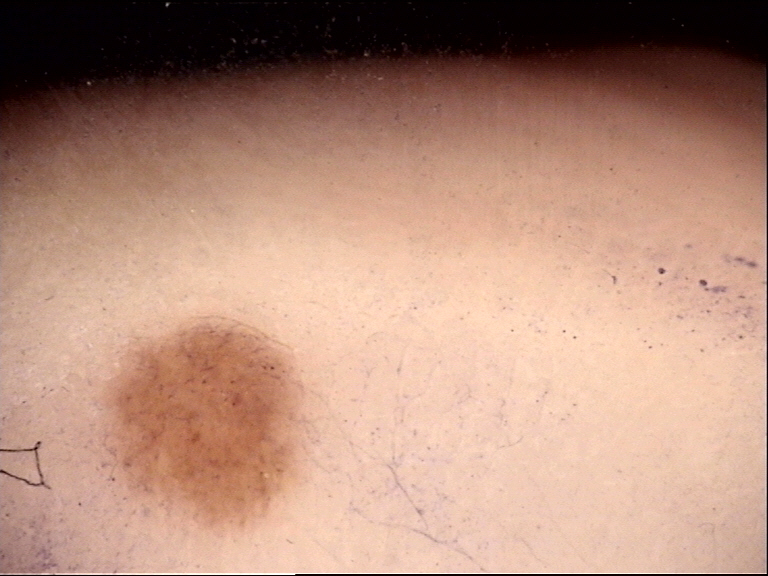  diagnosis:
    name: junctional nevus
    code: jb
    malignancy: benign
    super_class: melanocytic
    confirmation: expert consensus